A dermoscopic photograph of a skin lesion.
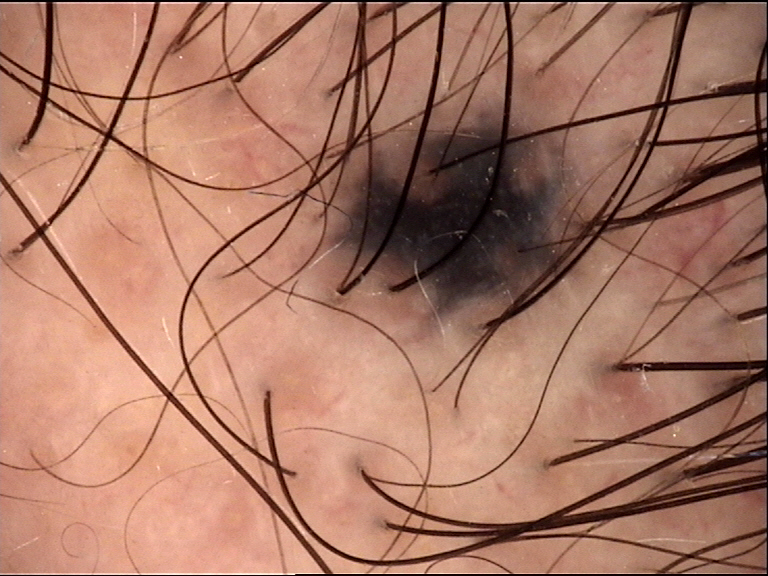The morphology is that of a banal, dermal lesion. Classified as a blue nevus.